The contributor is a male aged 30–39, close-up view, located on the arm and leg:
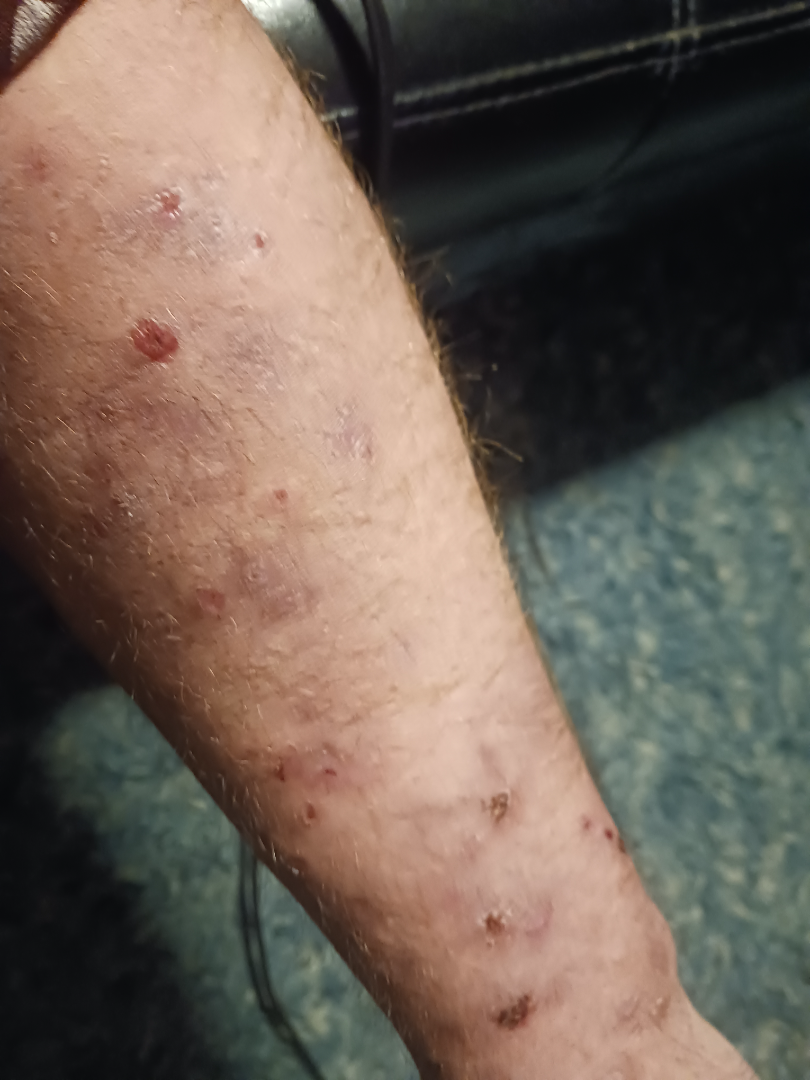Review:
Diagnostic features were not clearly distinguishable in this photograph.